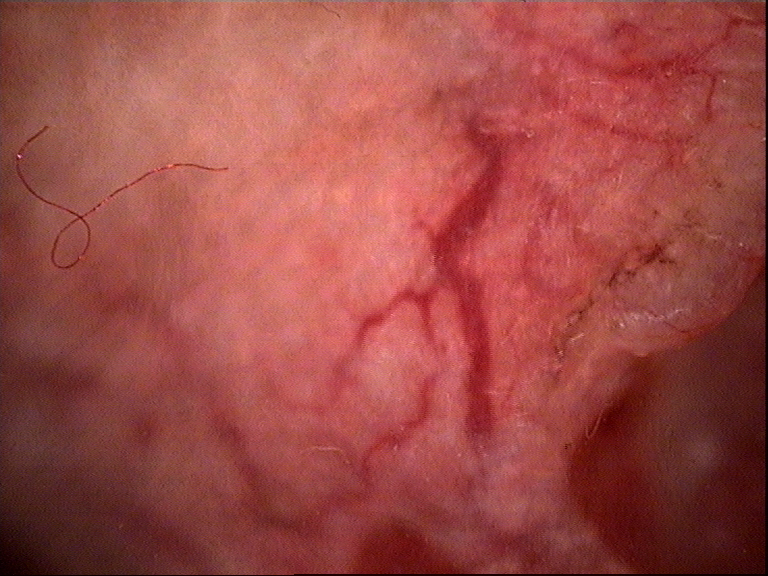Q: What is the diagnosis?
A: basal cell carcinoma (biopsy-proven)